A clinical photograph showing a skin lesion in context · a female patient aged 78 to 82 — 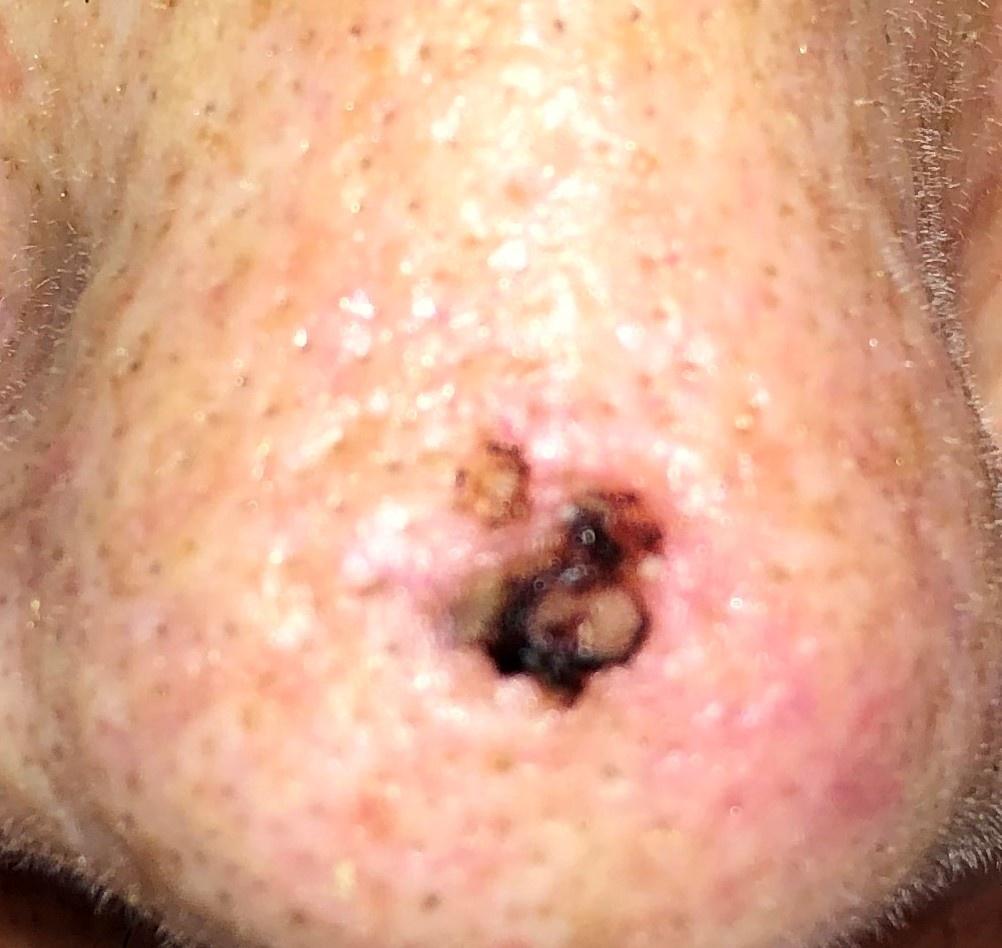<record>
  <lesion_location>
    <region>the head or neck</region>
  </lesion_location>
  <diagnosis>
    <name>Basal cell carcinoma</name>
    <malignancy>malignant</malignancy>
    <confirmation>histopathology</confirmation>
    <lineage>adnexal</lineage>
  </diagnosis>
</record>